The affected area is the front of the torso; the photo was captured at an angle — 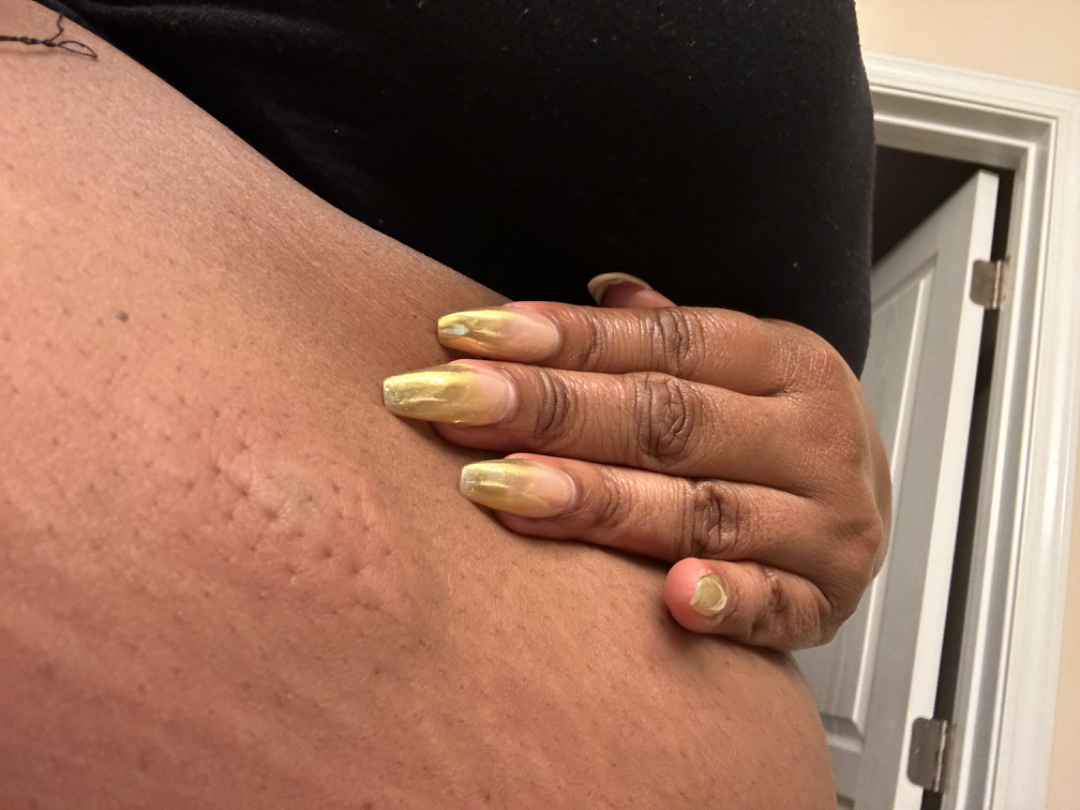{
  "skin_tone": {
    "fitzpatrick": "V",
    "monk_skin_tone": [
      4,
      6
    ]
  },
  "duration": "less than one week",
  "patient_category": "a rash",
  "symptoms": [
    "burning",
    "bothersome appearance",
    "pain"
  ],
  "texture": "raised or bumpy",
  "differential": {
    "leading": [
      "Insect Bite"
    ],
    "considered": [
      "Geographic tongue"
    ],
    "unlikely": [
      "Urticaria"
    ]
  }
}